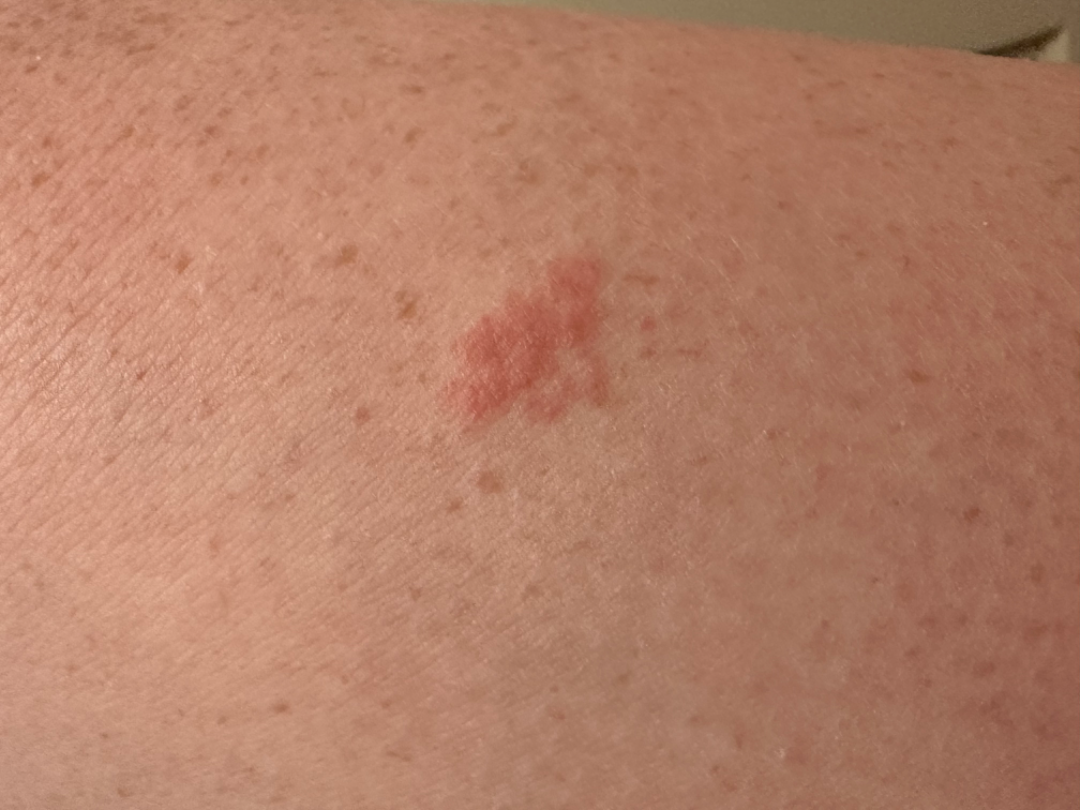assessment — indeterminate from the photograph | patient describes the issue as — a rash | subject — female, age 18–29 | described texture — raised or bumpy | image framing — close-up | site — leg | lesion symptoms — none reported | skin tone — human graders estimated a Monk skin tone scale of 3.